A dermoscopy image of a single skin lesion: 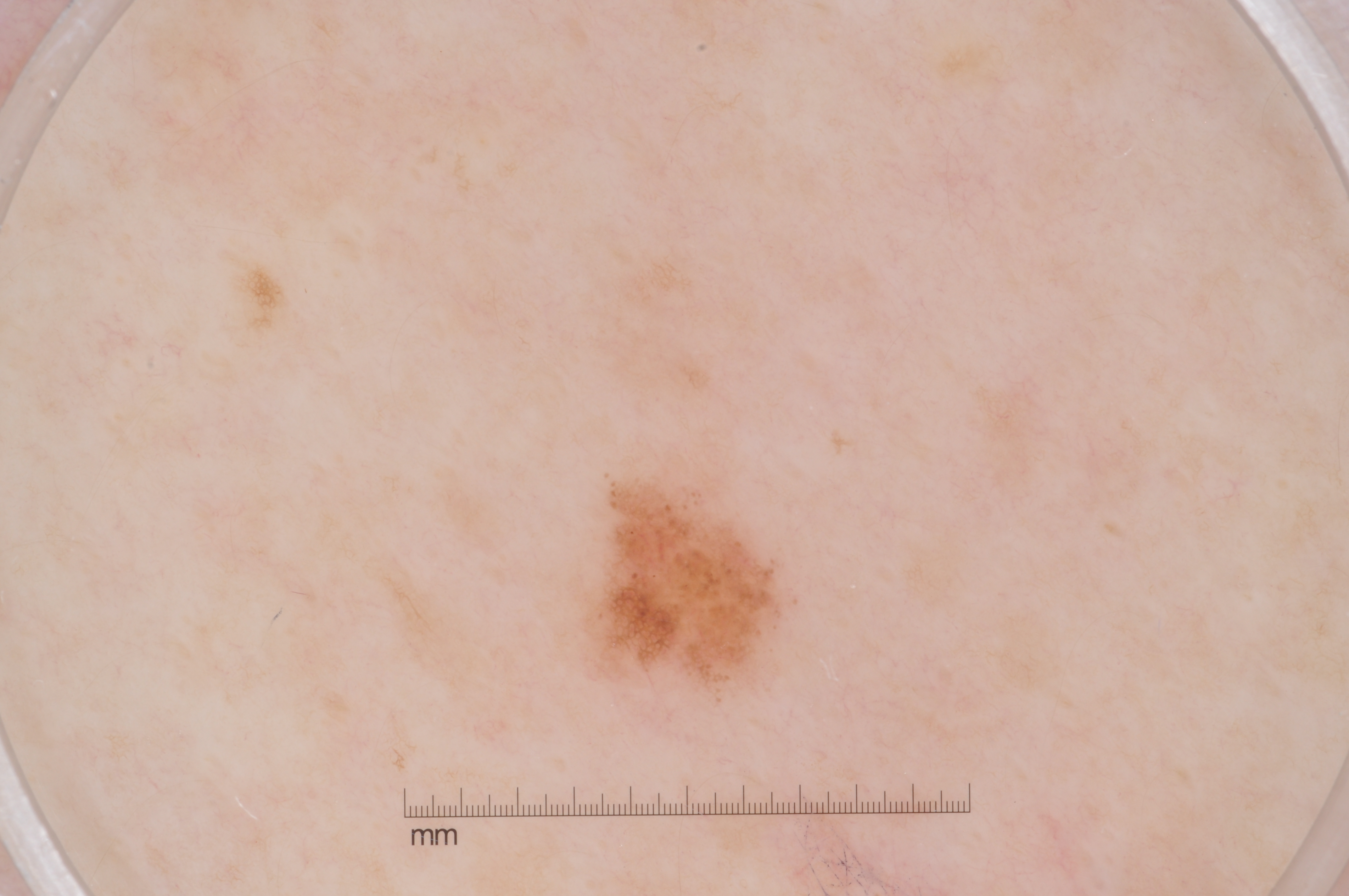Summary: Dermoscopic assessment notes milia-like cysts and pigment network. The lesion occupies the region x1=579 y1=471 x2=786 y2=703. Conclusion: Expert review diagnosed this as a melanocytic nevus.